A skin lesion imaged with a dermatoscope: 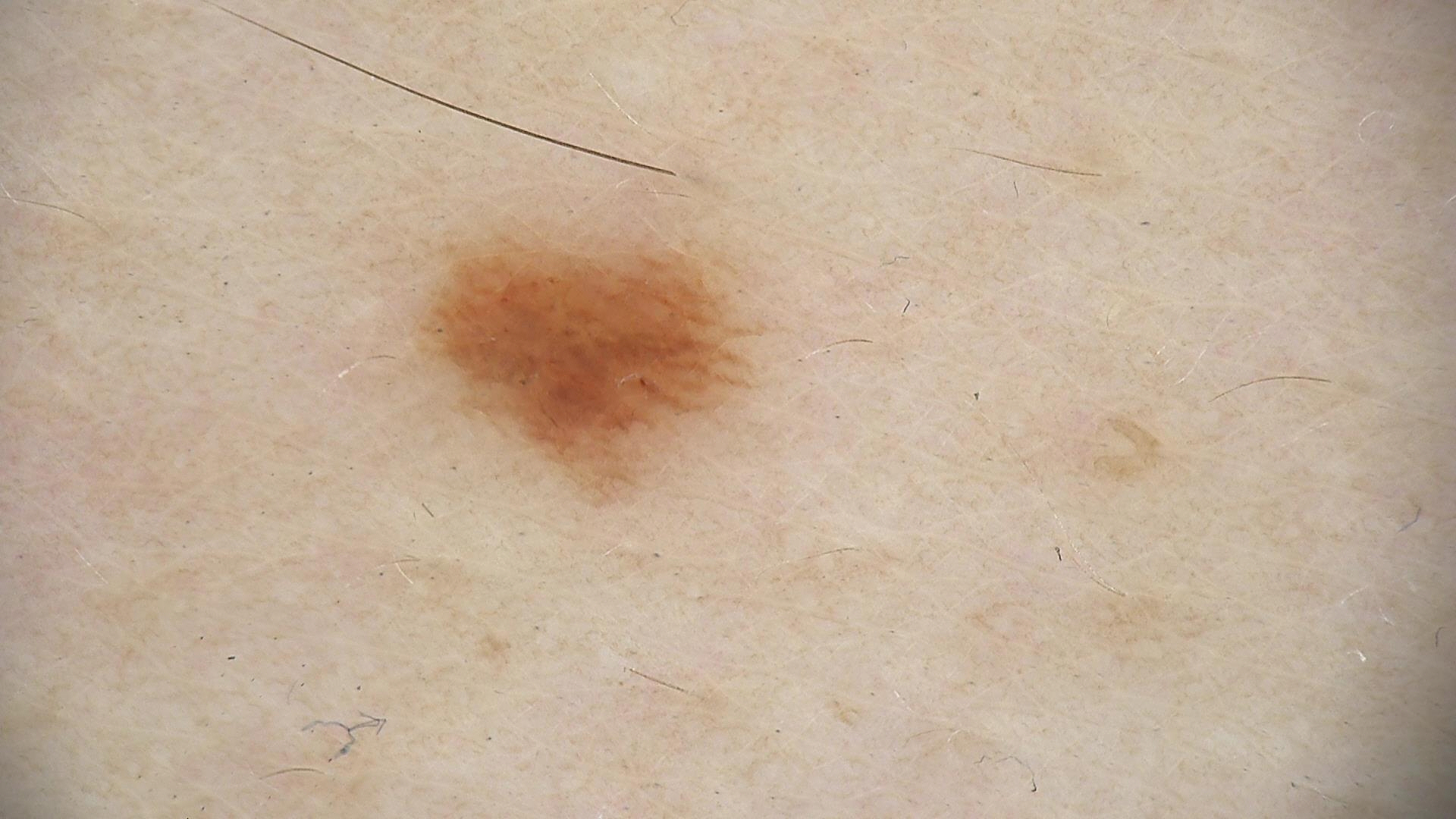The diagnosis was a benign lesion — a dysplastic junctional nevus.